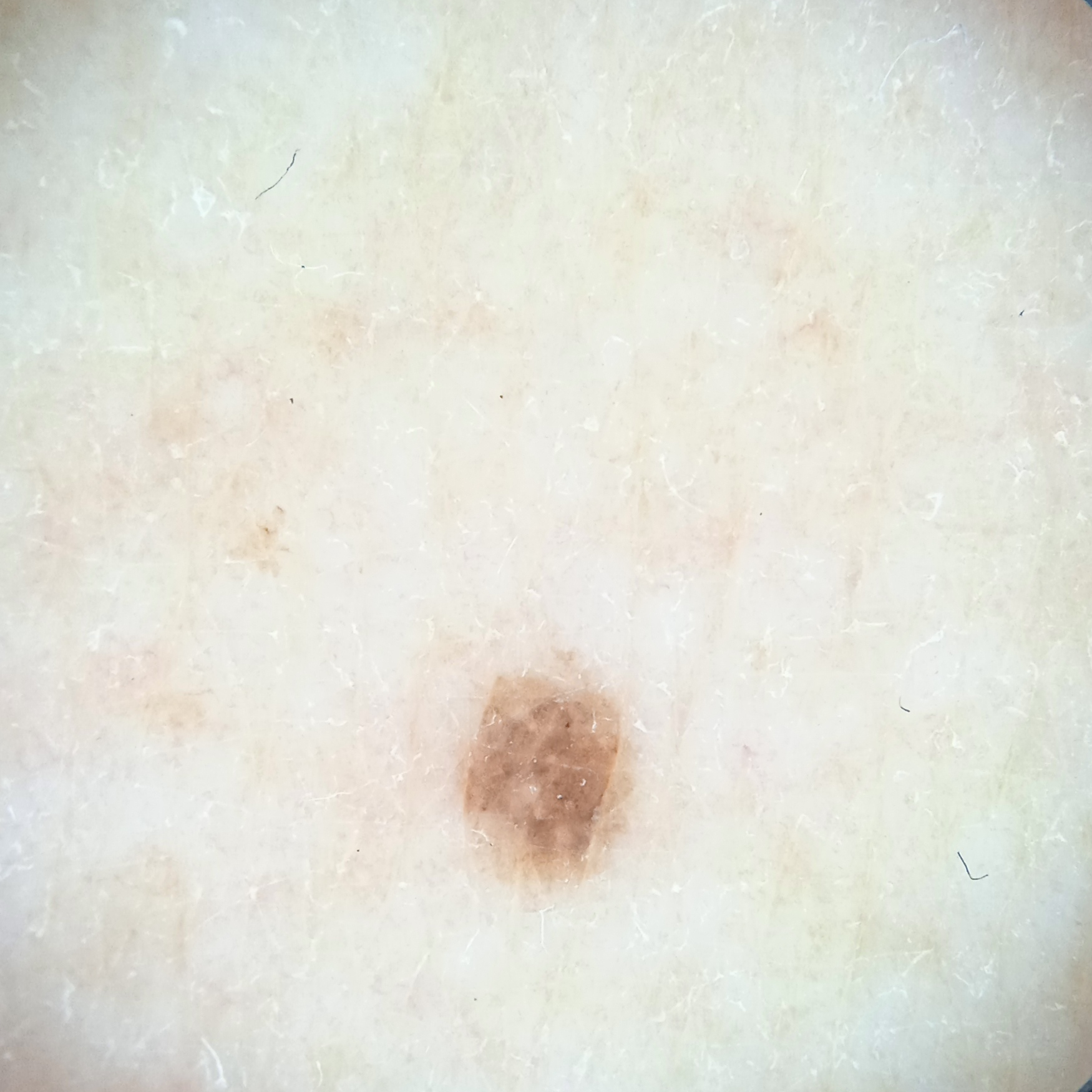A skin lesion imaged with a dermatoscope. The patient reports a personal history of skin cancer. A female patient age 50. The patient says their skin reddens with sun exposure. A moderate number of moles by the patient's own estimate. The lesion is on an arm. The lesion is about 2.5 mm across. The dermatologists' assessment was a melanocytic nevus.